Reported duration is less than one week. Located on the back of the hand. Female subject, age 18–29. The lesion is described as raised or bumpy and rough or flaky. The patient considered this a rash. Close-up view. The patient did not report lesion symptoms: 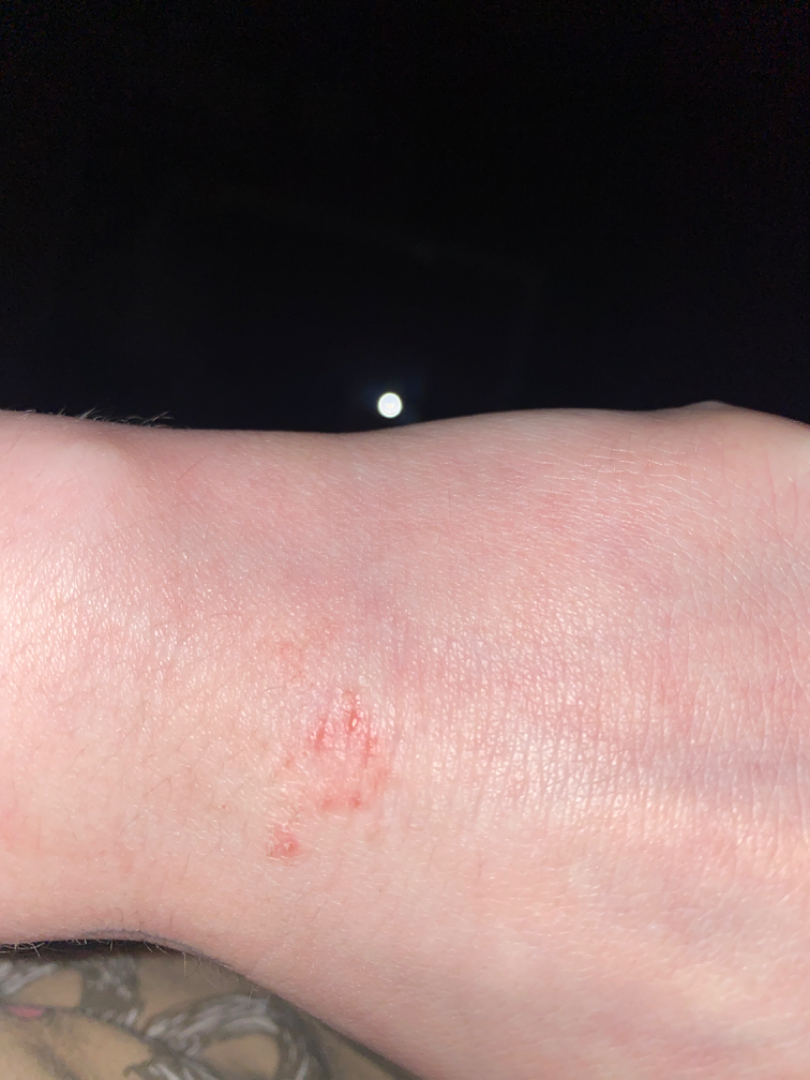Assessment:
On photographic review, favoring Allergic Contact Dermatitis; the differential also includes Irritant Contact Dermatitis.